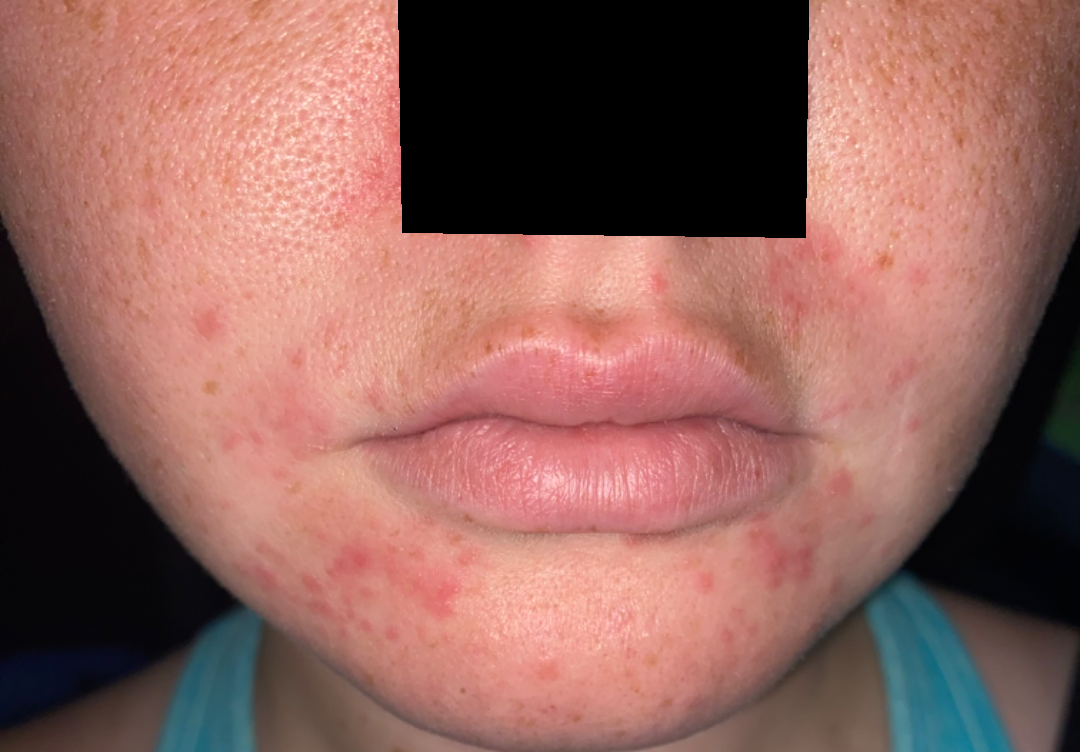- self-categorized as: a rash
- reported symptoms: none reported
- skin tone: Fitzpatrick skin type III; human graders estimated MST 2 or 3
- framing: close-up
- site: head or neck
- onset: one to three months
- dermatologist impression: in keeping with Perioral Dermatitis